A dermoscopic close-up of a skin lesion:
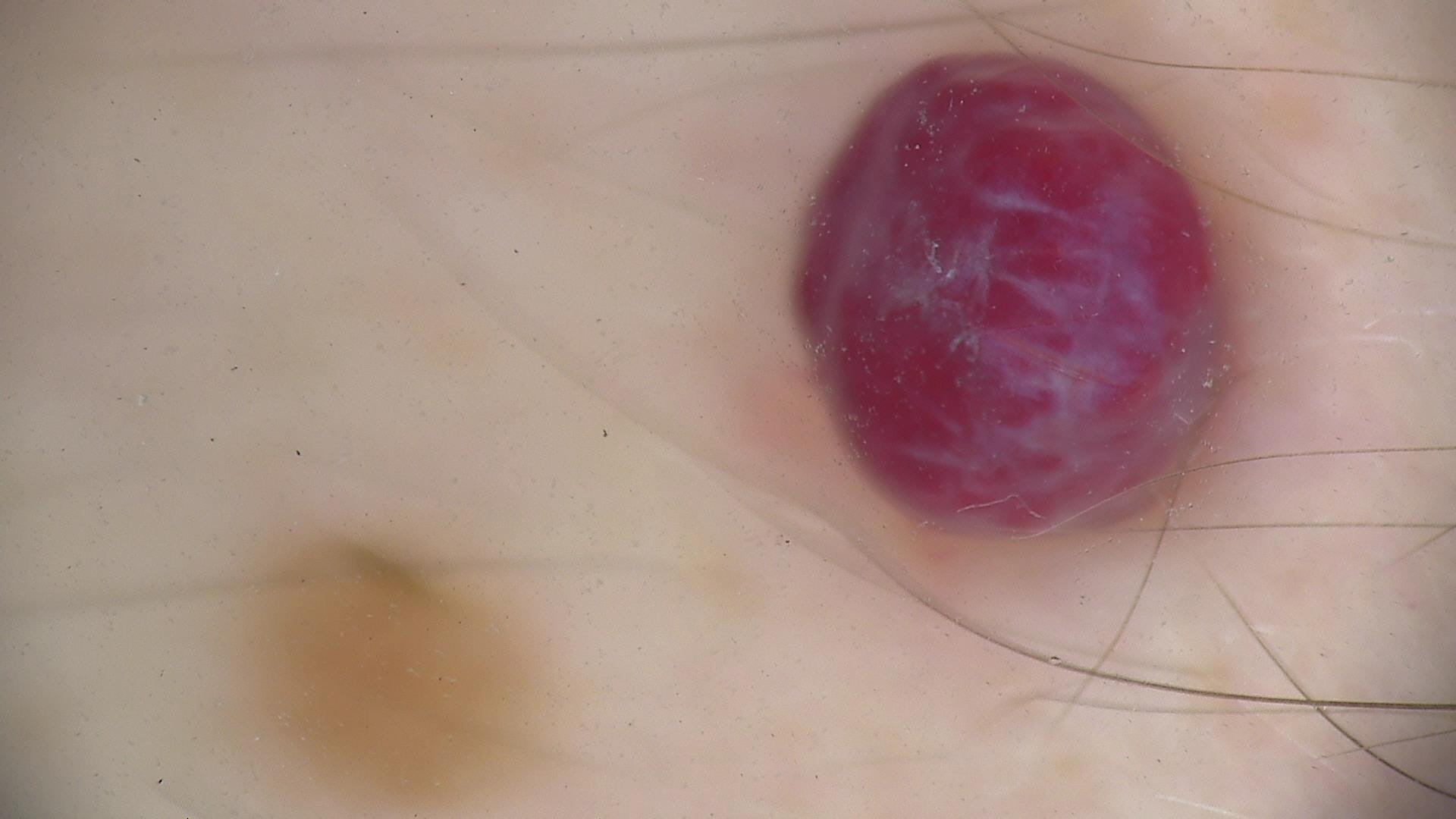Q: What kind of lesion is this?
A: vascular
Q: What is the diagnosis?
A: hemangioma (expert consensus)